An overview clinical photograph of a skin lesion. A female subject in their mid- to late 60s — 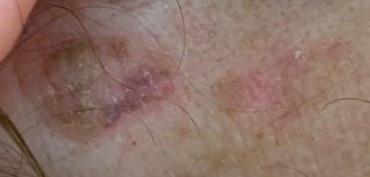On biopsy, the diagnosis was a malignant lesion — a basal cell carcinoma.